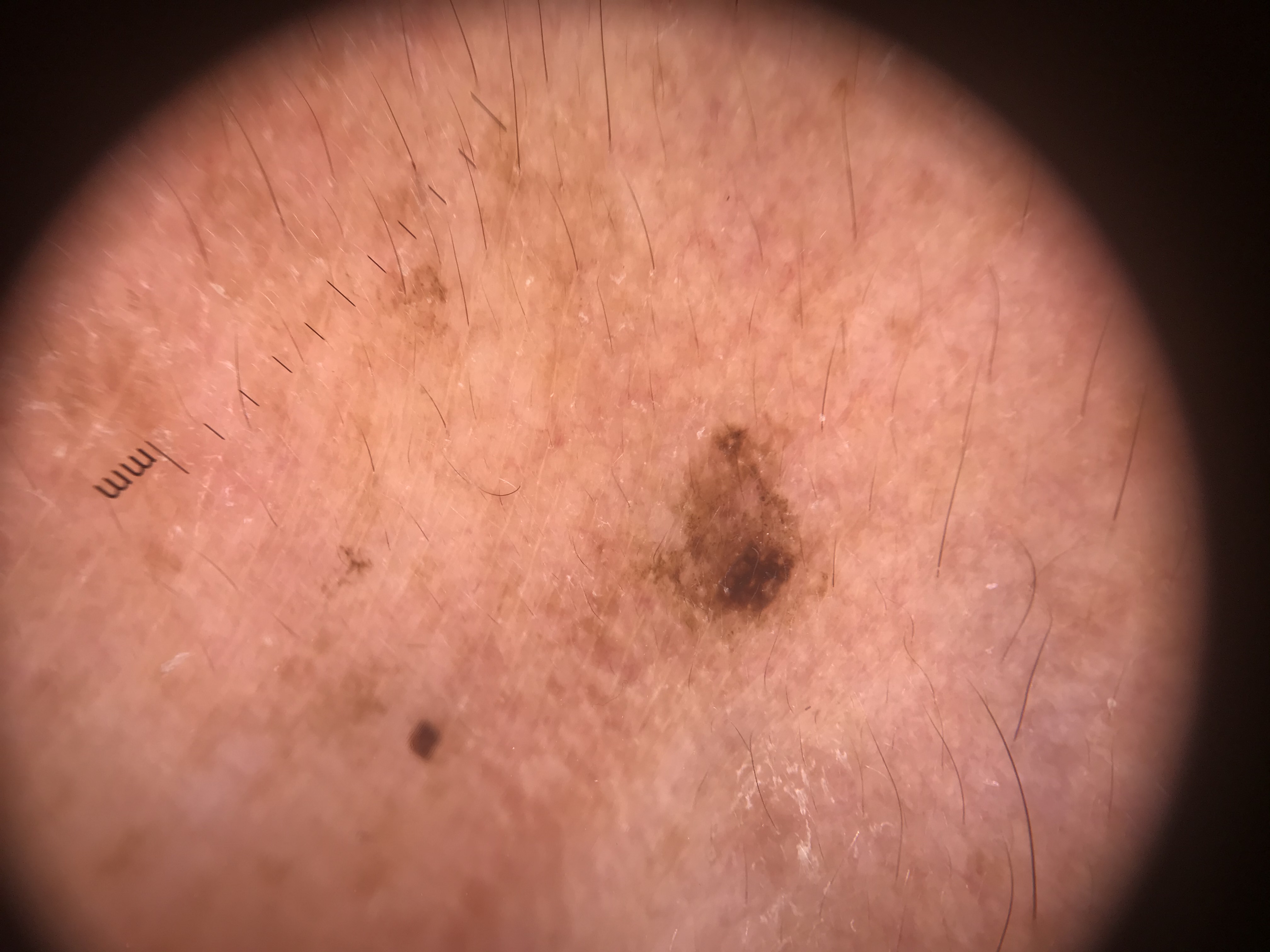label: seborrheic keratosis (expert consensus).